The patient also reports fatigue and shortness of breath. The leg is involved. Self-categorized by the patient as a rash. Fitzpatrick III. The subject is 60–69, male. This is a close-up image. The lesion is associated with itching and bothersome appearance. The lesion is described as rough or flaky. Reported duration is more than five years — 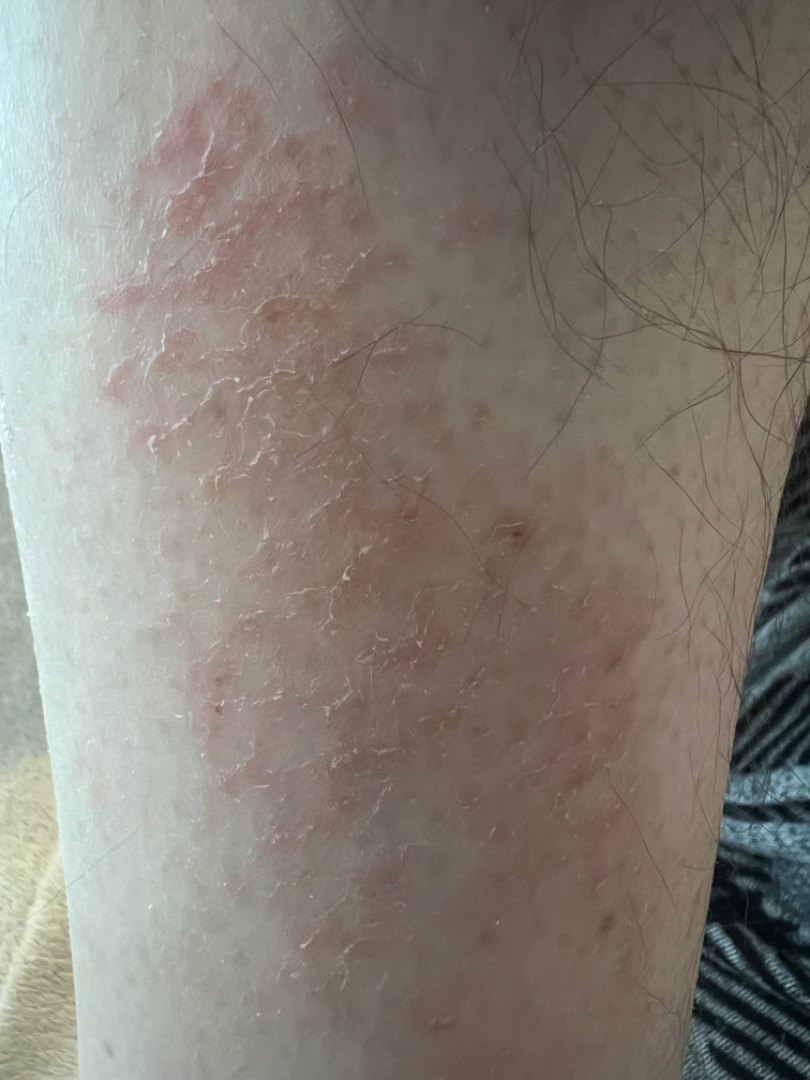assessment=Eczema (primary).